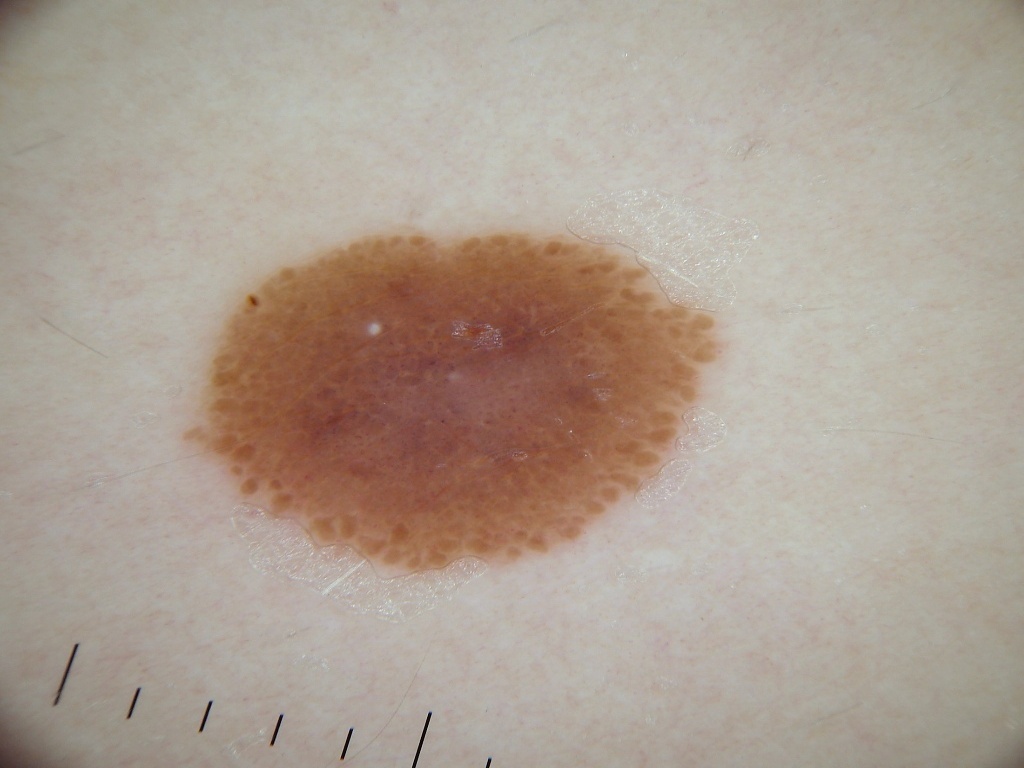Summary: A dermoscopic image of a skin lesion. A female patient about 15 years old. On dermoscopy, the lesion shows negative network, globules, and milia-like cysts. A mid-sized lesion within the field. The visible lesion spans 176/228/718/573. Conclusion: Clinically diagnosed as a melanocytic nevus, a benign lesion.